A dermoscopic image of a skin lesion.
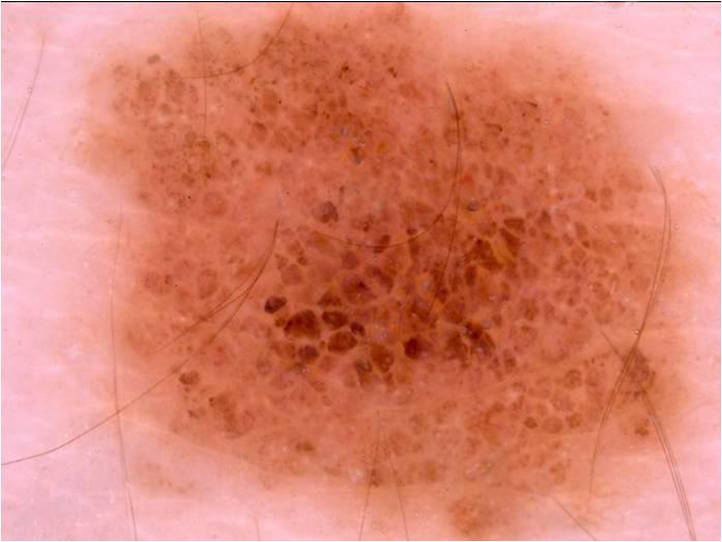Lesion location: x1=66, y1=3, x2=716, y2=540. The lesion takes up a large portion of the image. Expert review diagnosed this as a benign lesion.